A patient in their 70s: 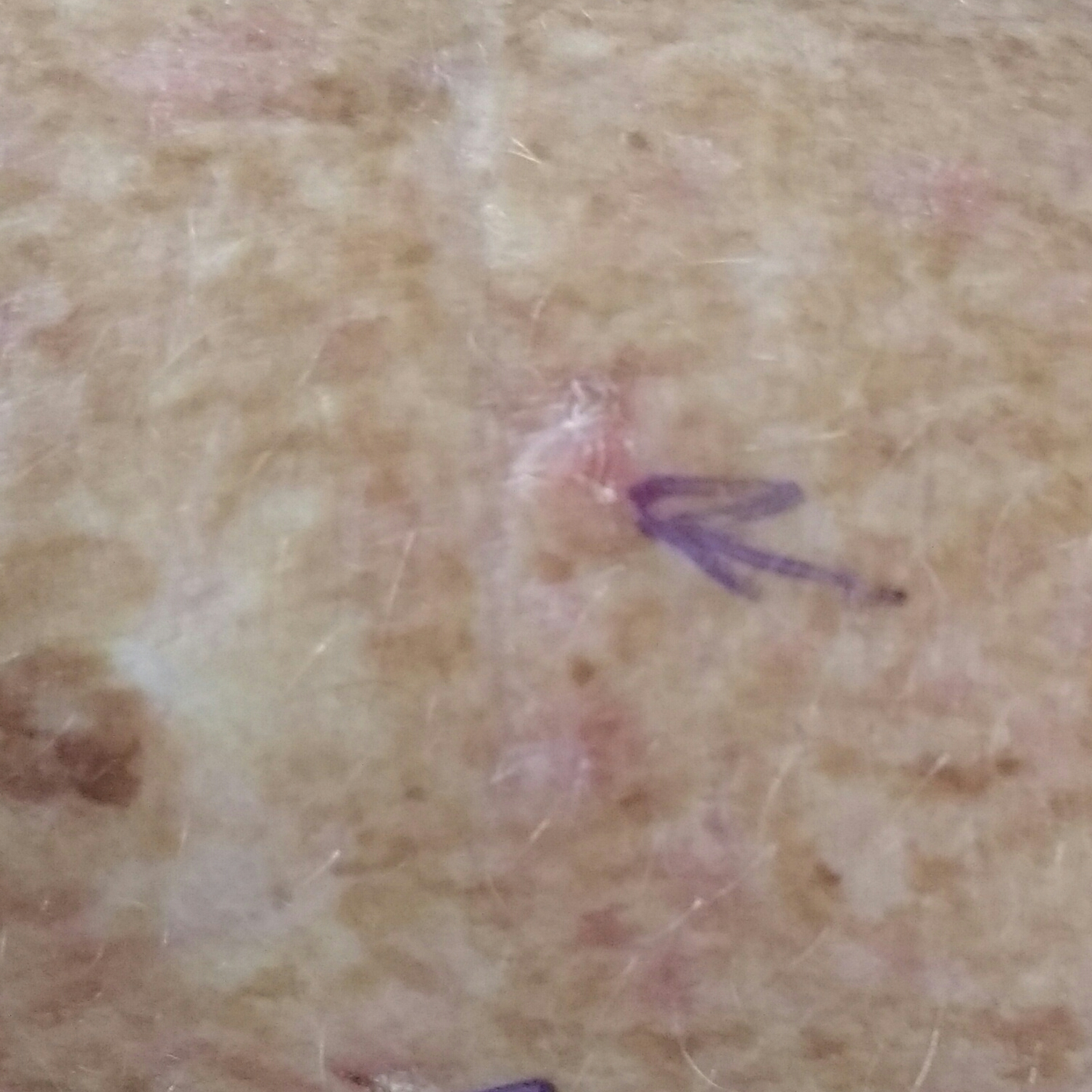Case summary: The lesion was found on a forearm. Per patient report, the lesion itches and is elevated, but has not changed. Conclusion: The diagnostic impression was an actinic keratosis.